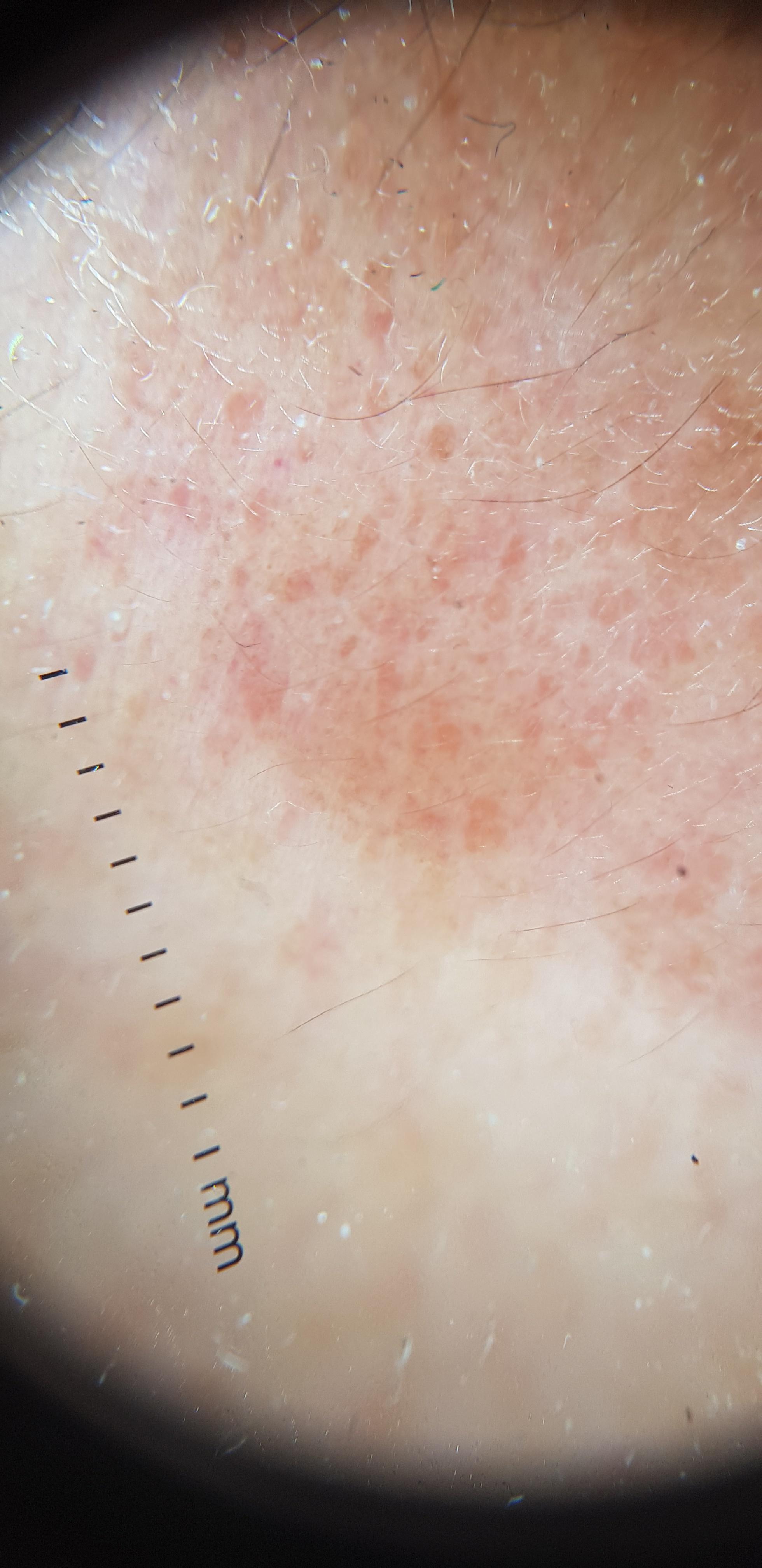{
  "image": "contact-polarized dermoscopy",
  "lesion_location": {
    "region": "the head or neck"
  },
  "diagnosis": {
    "name": "Solar or actinic keratosis",
    "malignancy": "indeterminate",
    "confirmation": "histopathology",
    "lineage": "epidermal"
  }
}